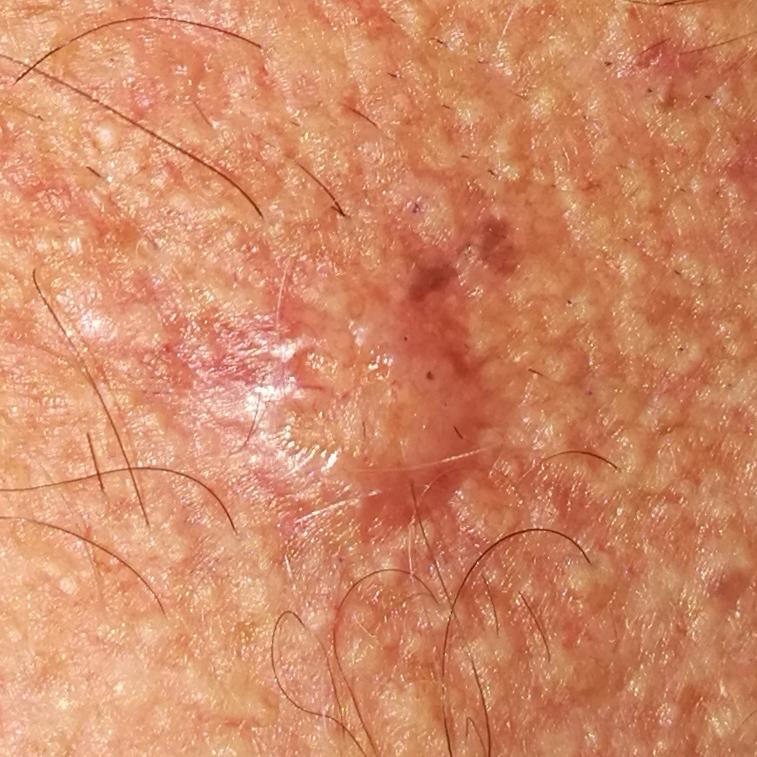Findings:
* exposures · no tobacco use, no alcohol use
* imaging · clinical photo
* FST · II
* patient · male, 80 years of age
* body site · the neck
* diameter · 5 × 5 mm
* symptoms · growth, itching, elevation
* diagnostic label · basal cell carcinoma (biopsy-proven)